The patient is a male approximately 70 years of age, a dermoscopic view of a skin lesion:
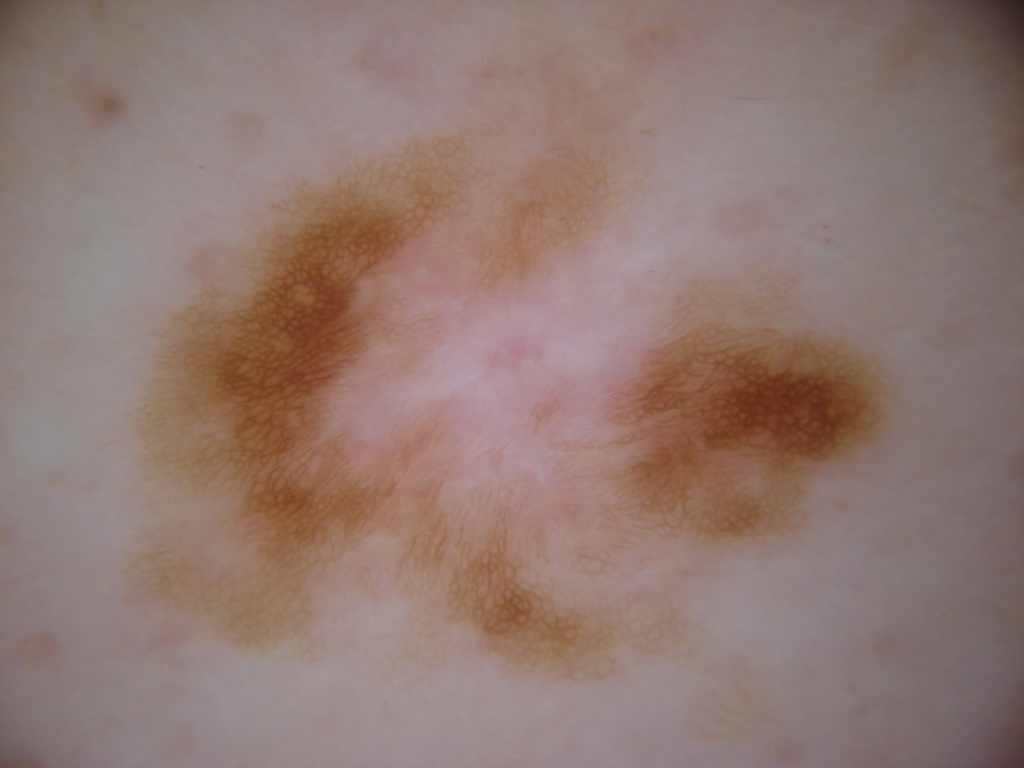Summary: Dermoscopy demonstrates pigment network, with no negative network, globules, milia-like cysts, or streaks. The lesion occupies roughly 50% of the field. With coordinates (x1, y1, x2, y2), the lesion occupies the region 114 83 902 700. Impression: Expert review diagnosed this as a melanocytic nevus, a benign lesion.